The patient considered this skin that appeared healthy to them · the lesion involves the leg · present for about one day · the subject is female · no associated lesion symptoms were reported · the photograph was taken at a distance · the lesion is described as flat — 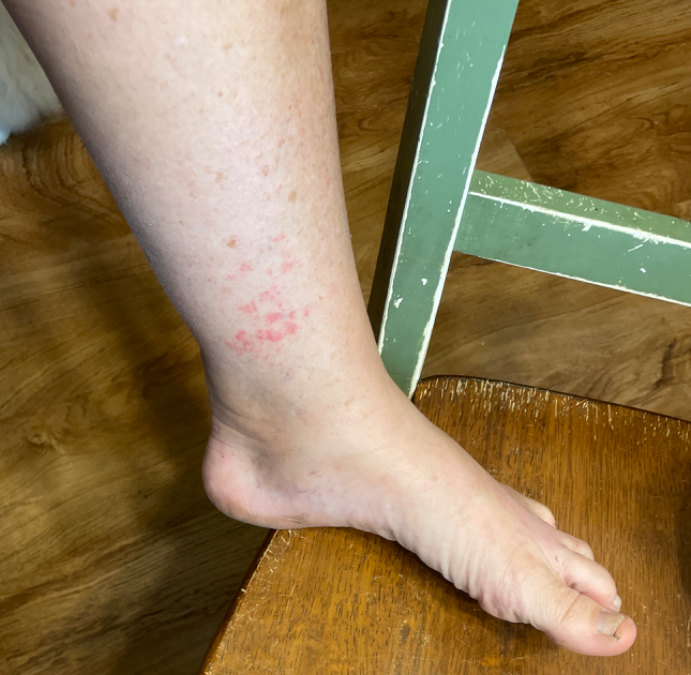Findings:
- clinical impression: Allergic Contact Dermatitis (possible); Stasis Dermatitis (possible); Eczema (possible); Contact dermatitis (possible)